The photograph was taken at an angle · located on the sole of the foot · female patient, age 40–49 — 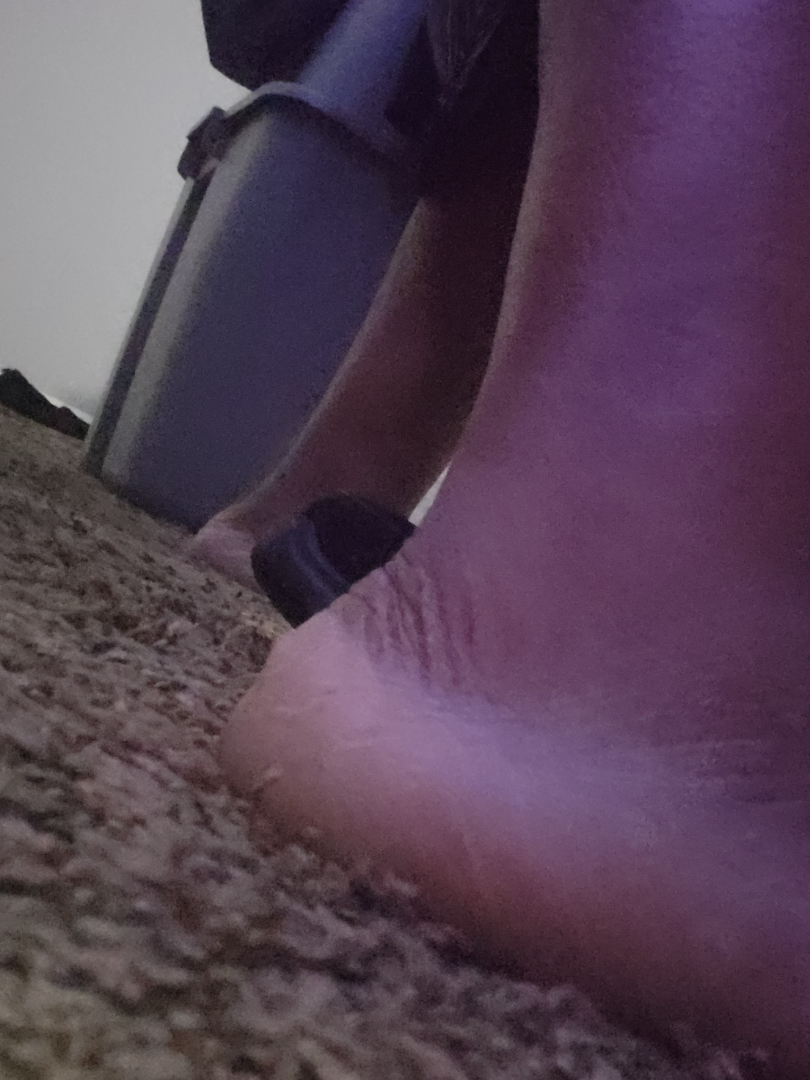On dermatologist assessment of the image, Tinea (weight 0.41); Eczema (weight 0.41); Psoriasis (weight 0.18).